A dermoscopic photograph of a skin lesion.
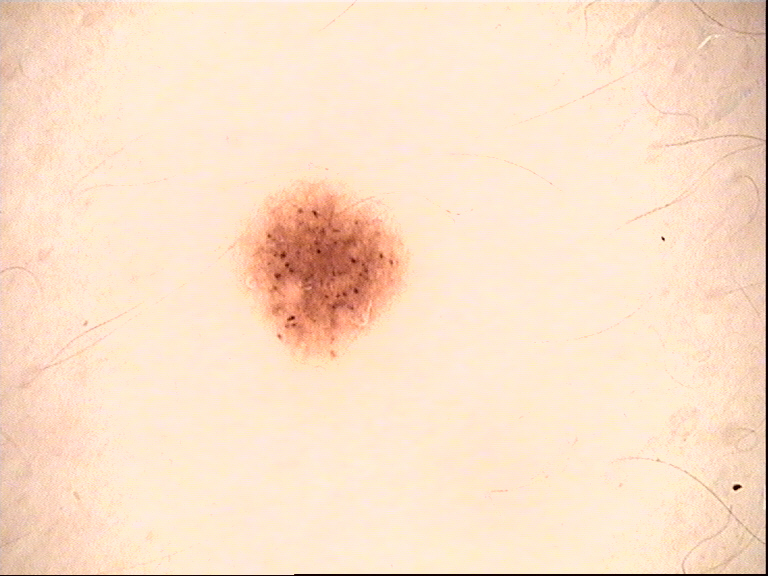Impression: The diagnosis was a dysplastic junctional nevus.